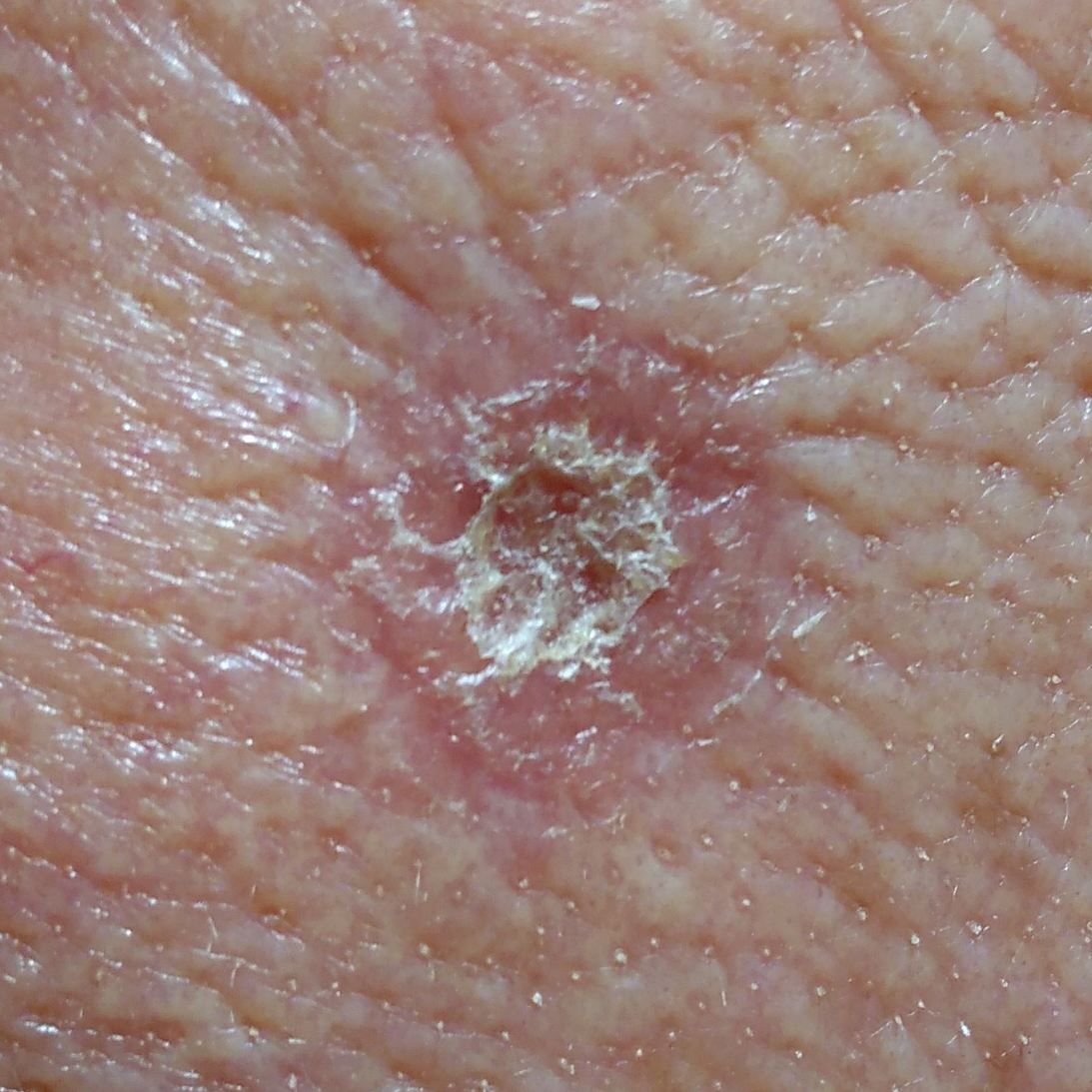The chart records no prior malignancy (patient or family). A clinical photograph of a skin lesion. The patient is skin type III. A female patient in their 70s. Located on the face. The lesion measures 10 × 9 mm. Per patient report, the lesion itches and has bled. Histopathology confirmed an actinic keratosis.